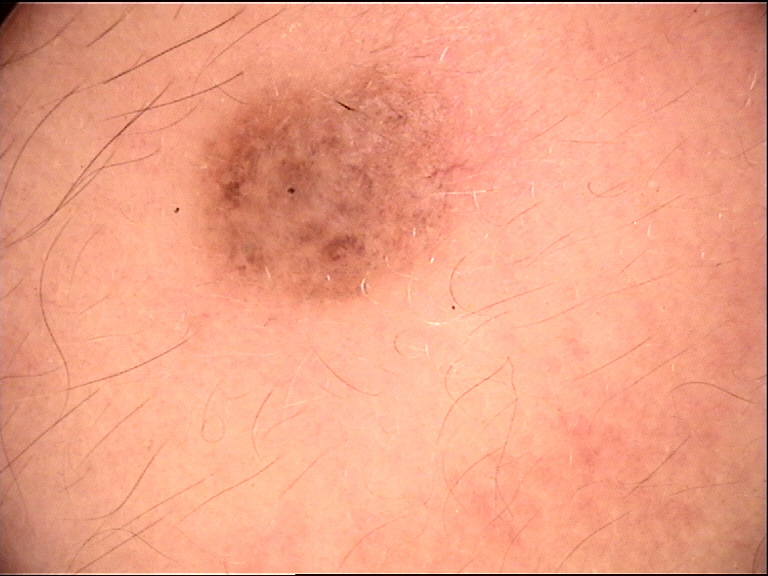A dermoscopic close-up of a skin lesion. The morphology is that of a banal lesion. Classified as a compound nevus.